An image taken at an angle:
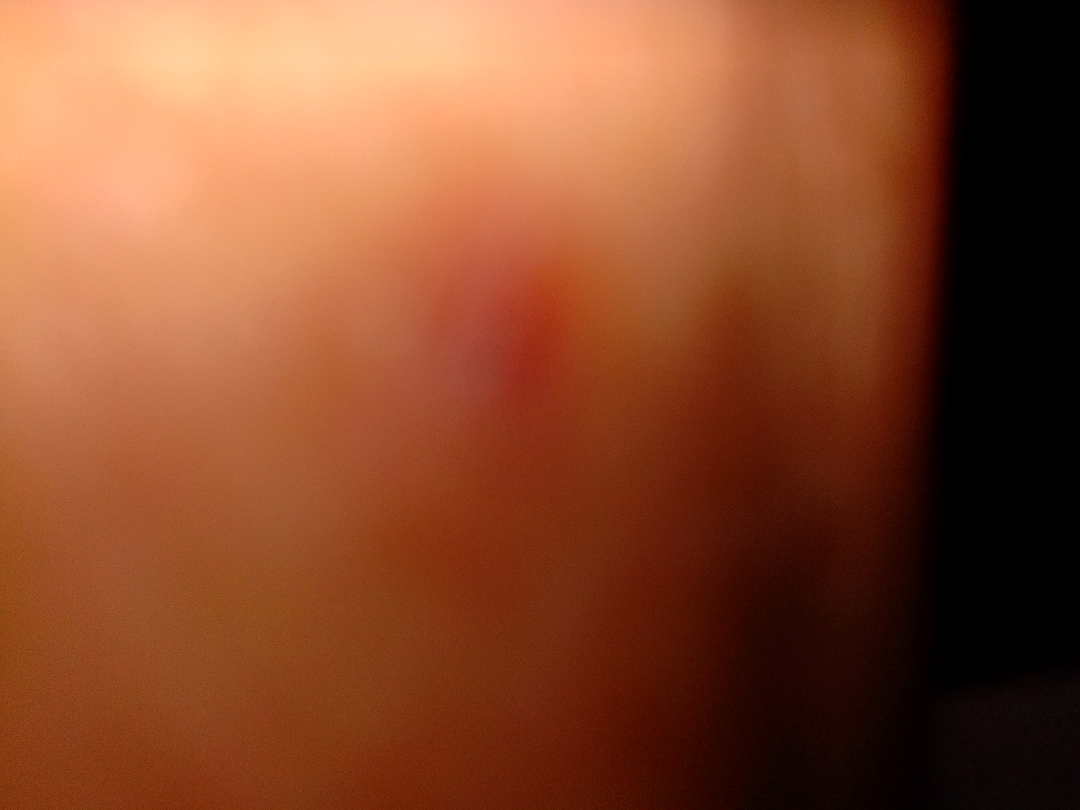Findings:
• clinical impression · most consistent with Insect Bite